A dermoscopic photograph of a skin lesion:
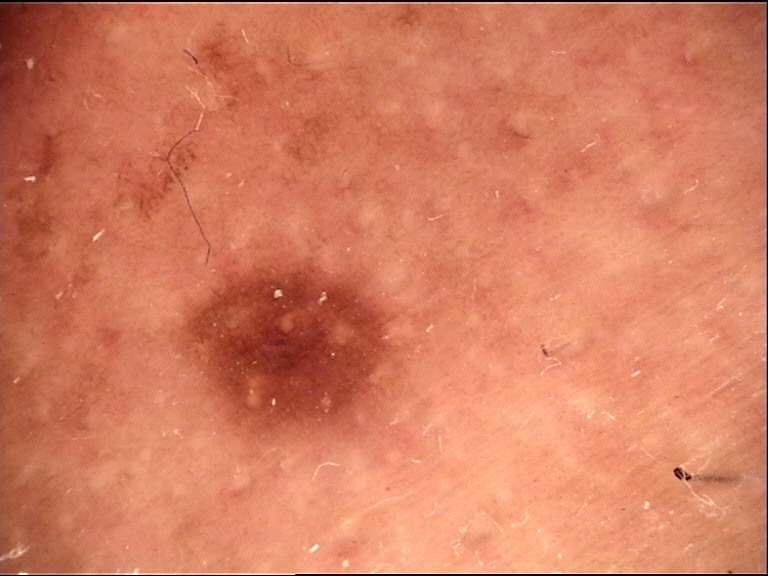The diagnosis was a dysplastic junctional nevus.